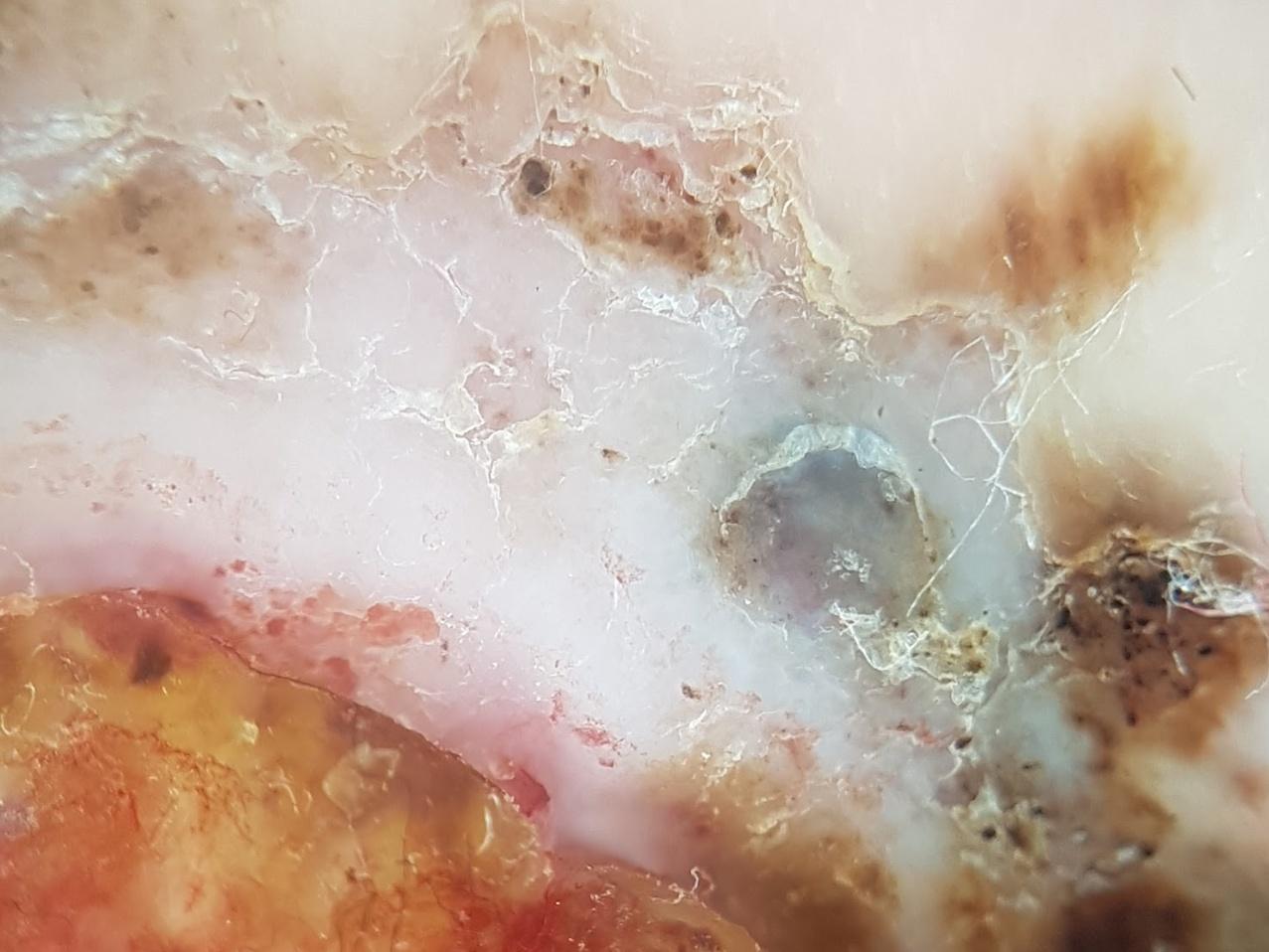<skin_lesion>
  <skin_type>II</skin_type>
  <patient>
    <age_approx>65</age_approx>
    <sex>male</sex>
  </patient>
  <melanoma_history>
    <personal_hx_melanoma>true</personal_hx_melanoma>
  </melanoma_history>
  <lesion_location>
    <region>an acral site (palms or soles)</region>
  </lesion_location>
  <diagnosis>
    <name>Melanoma</name>
    <malignancy>malignant</malignancy>
    <confirmation>histopathology</confirmation>
  </diagnosis>
</skin_lesion>